Few moles overall by the patient's own estimate. The patient says their skin reddens with sun exposure. Imaged for a research study, with no referral diagnosis recorded. A macroscopic clinical photograph of a skin lesion. A male subject aged 62 — 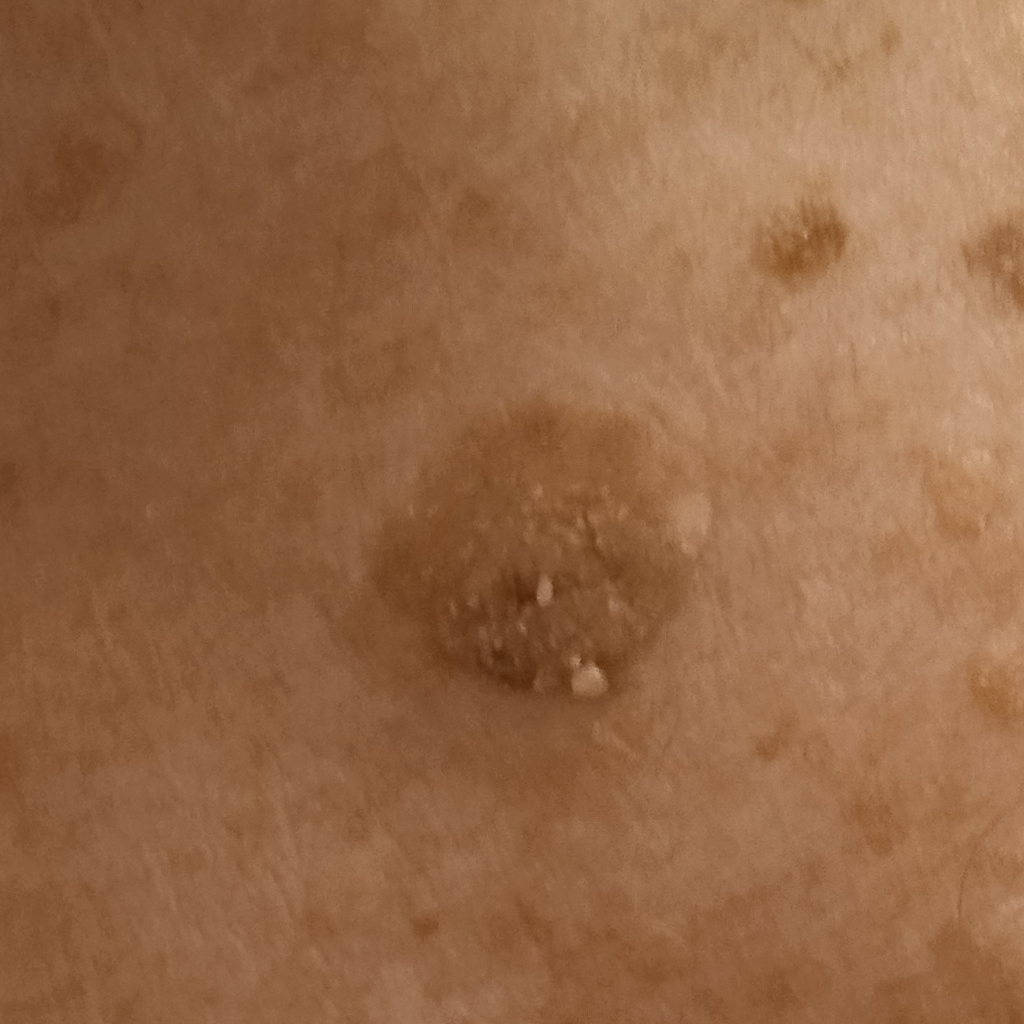lesion size: 11.3 mm; assessment: seborrheic keratosis (dermatologist consensus).